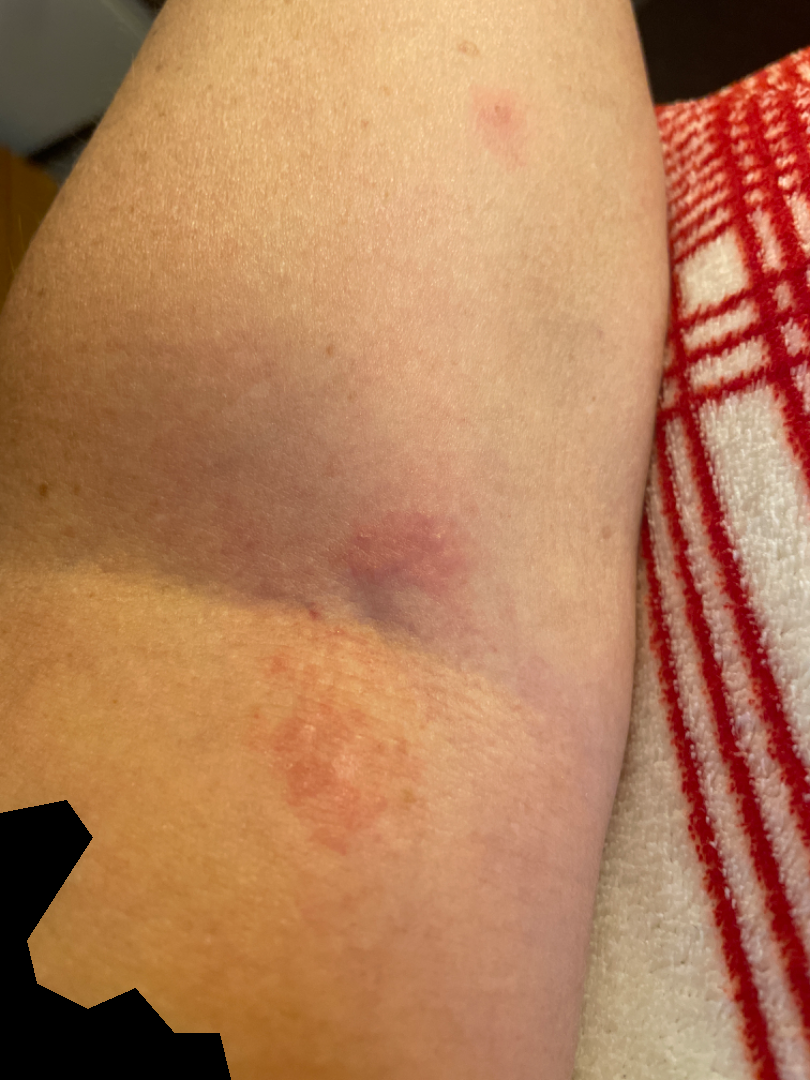<dermatology_case>
  <shot_type>close-up</shot_type>
  <differential>
    <leading>Eczema</leading>
  </differential>
</dermatology_case>